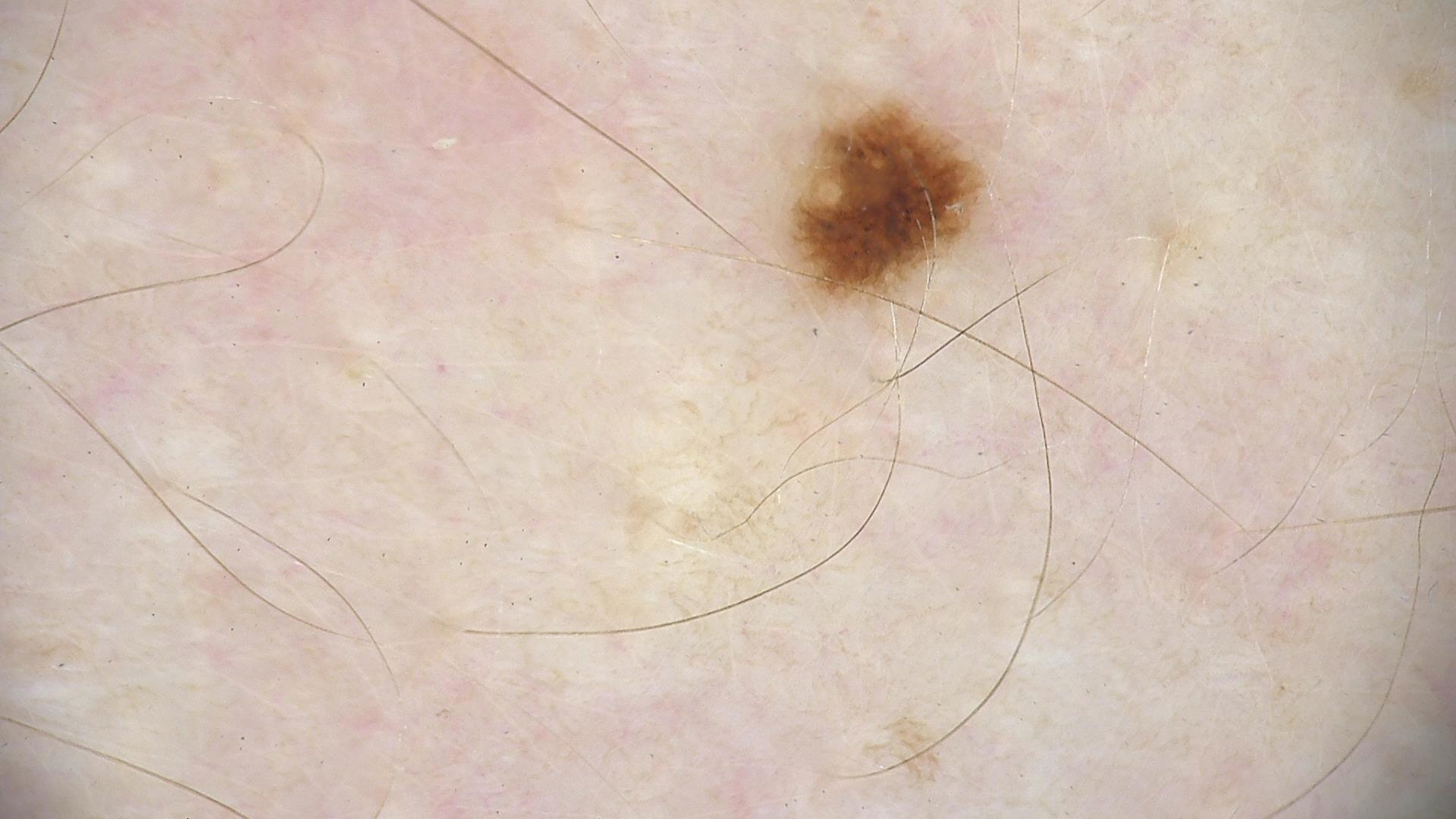image type = dermatoscopy; label = dysplastic junctional nevus (expert consensus).